A skin lesion imaged with a dermatoscope.
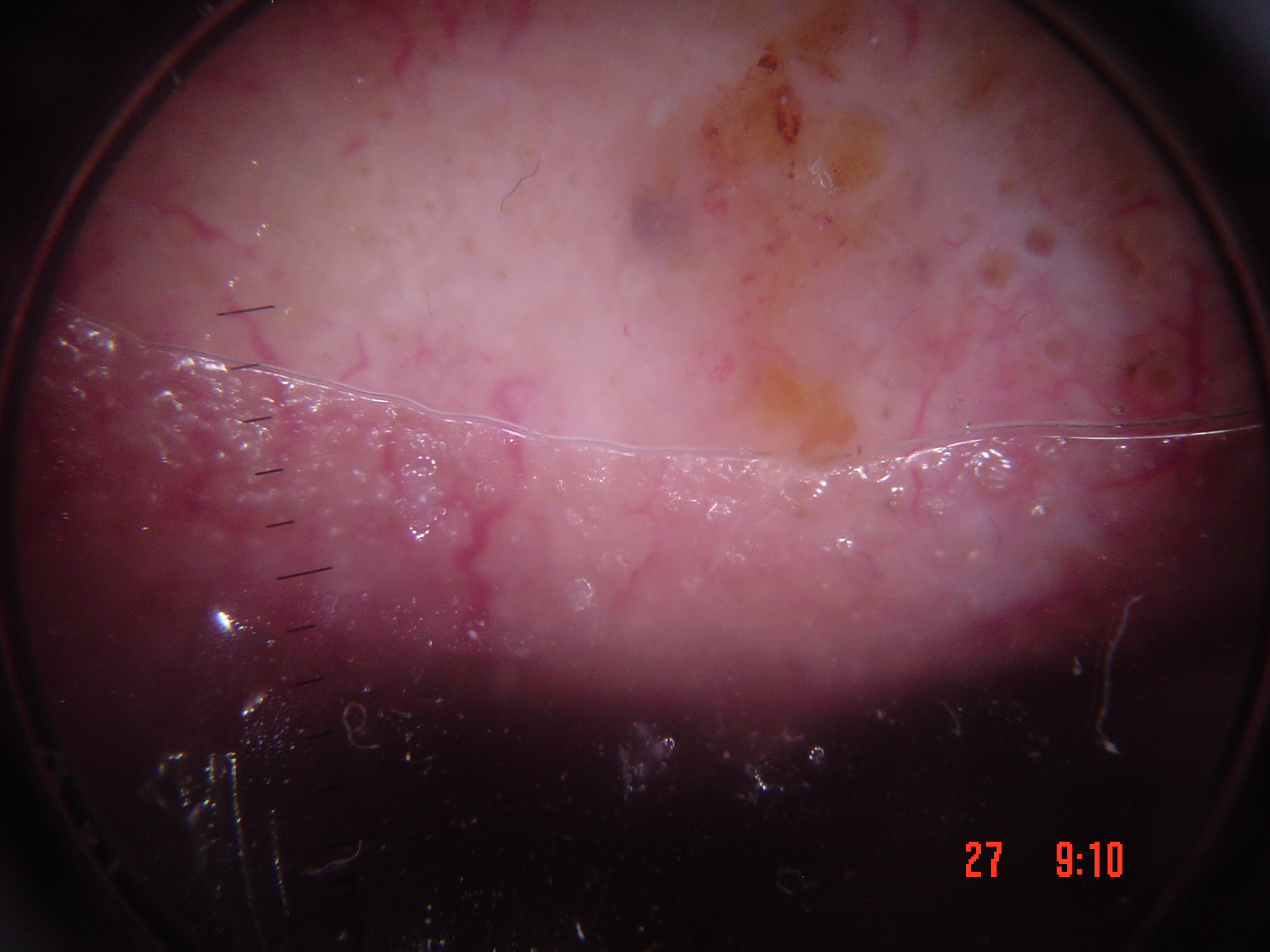{
  "lesion_type": {
    "main_class": "keratinocytic"
  },
  "diagnosis": {
    "name": "squamous cell carcinoma",
    "code": "scc",
    "malignancy": "malignant",
    "super_class": "non-melanocytic",
    "confirmation": "histopathology"
  }
}